A close-up photograph; female patient, age 70–79 — 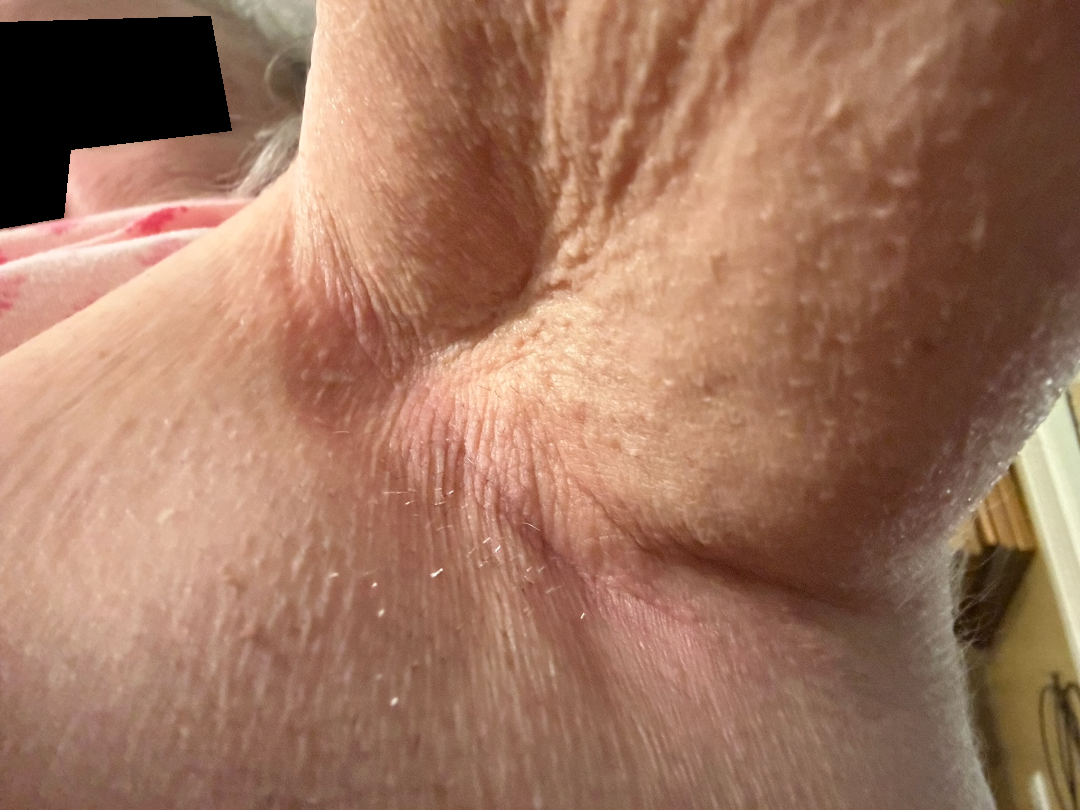Intertrigo (weight 0.33); Psoriasis (weight 0.33); Contact dermatitis, NOS (weight 0.33).